History notes no prior skin cancer (patient or family); a male subject 54 years of age; the patient was assessed as Fitzpatrick III; a clinical close-up photograph of a skin lesion — 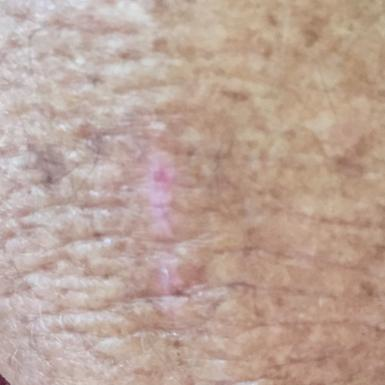site = an arm
size = approx. 4 × 3 mm
diagnostic label = actinic keratosis (clinical consensus)